A close-up photograph — 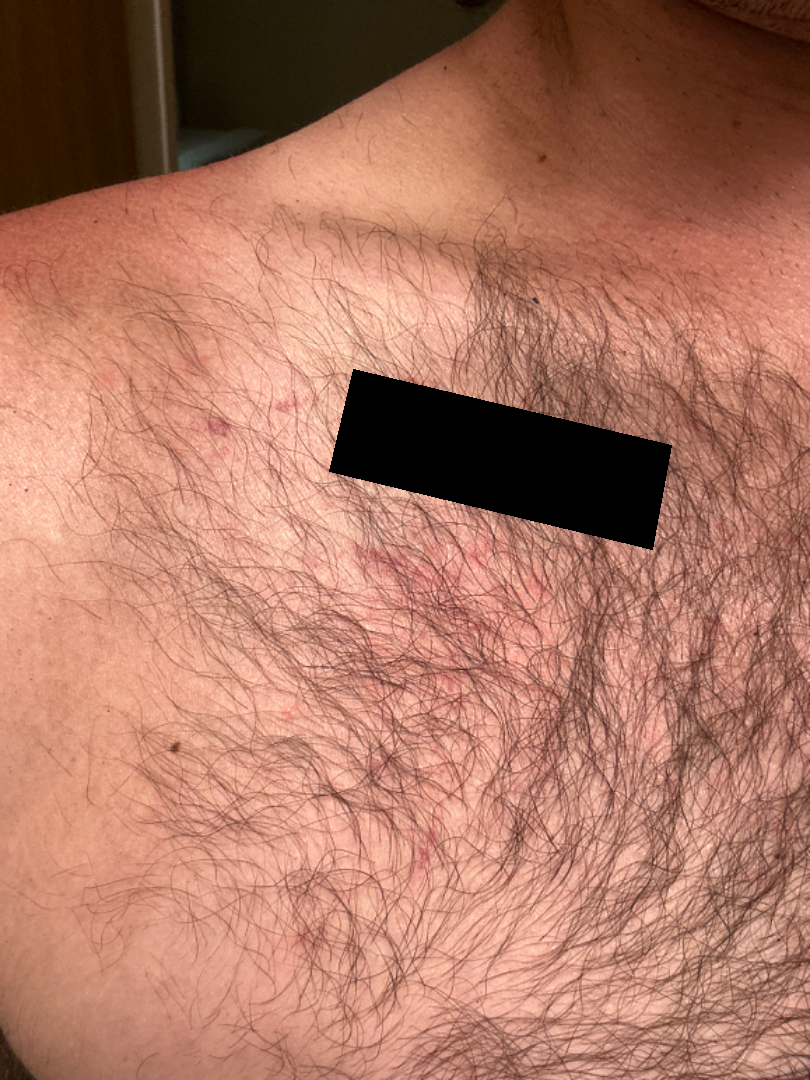No differential diagnosis could be assigned on photographic review.